A clinical photograph showing a skin lesion: 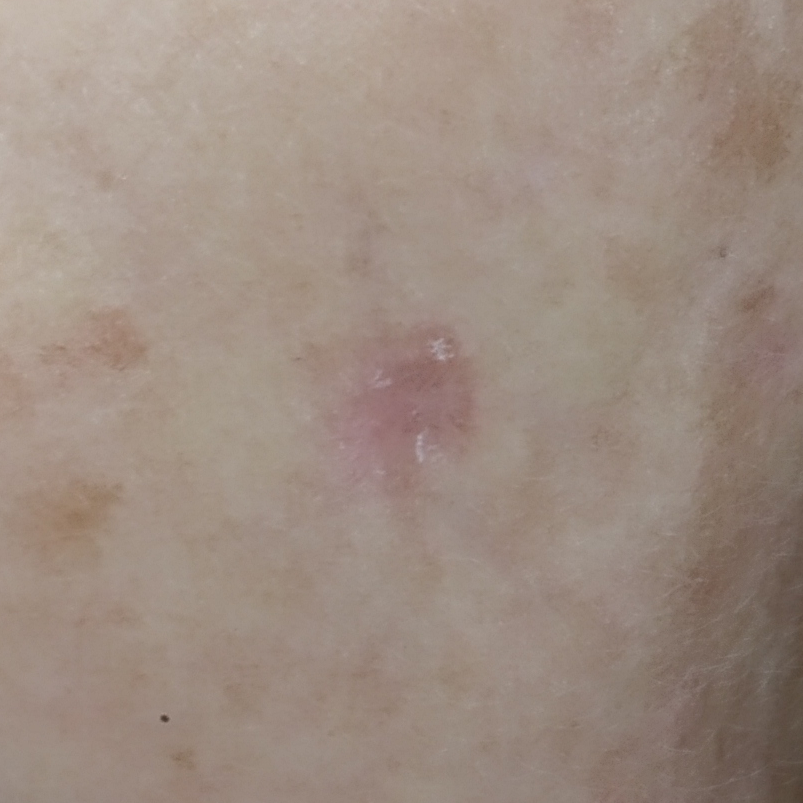The lesion involves the face. Histopathological examination showed an actinic keratosis.